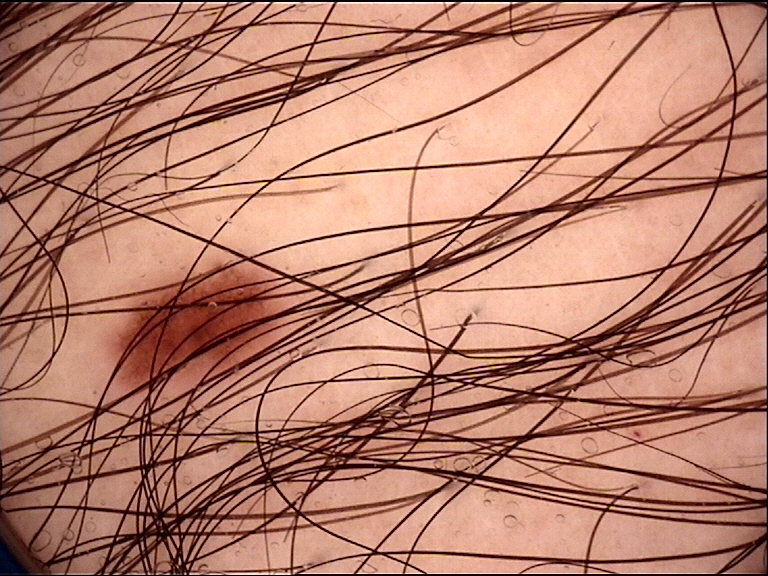Summary: A dermoscopic close-up of a skin lesion. Impression: Classified as a benign lesion — a dysplastic junctional nevus.